A male subject 65 years old.
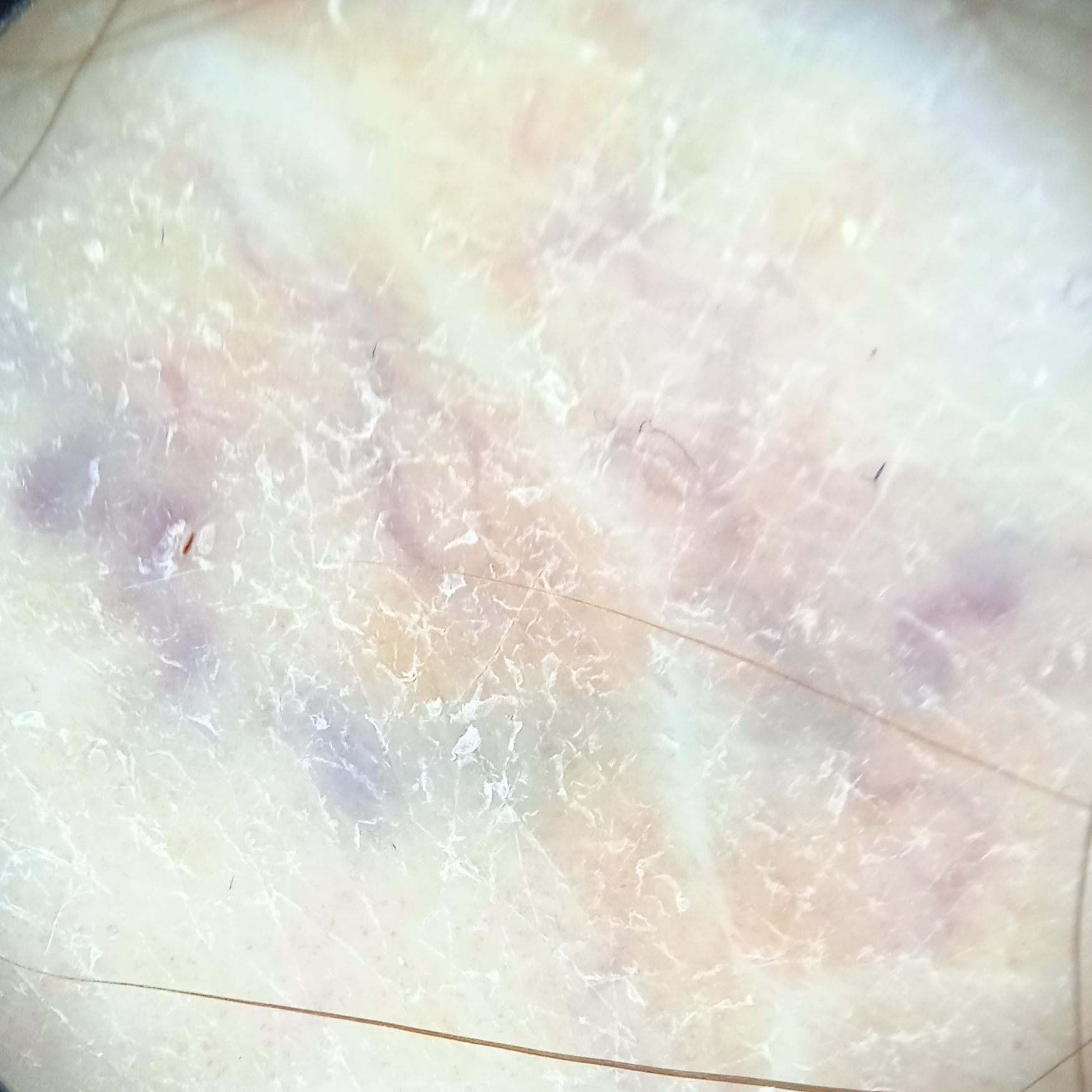Case:
• lesion size — 13 mm
• assessment — basal cell carcinoma (dermatologist consensus)